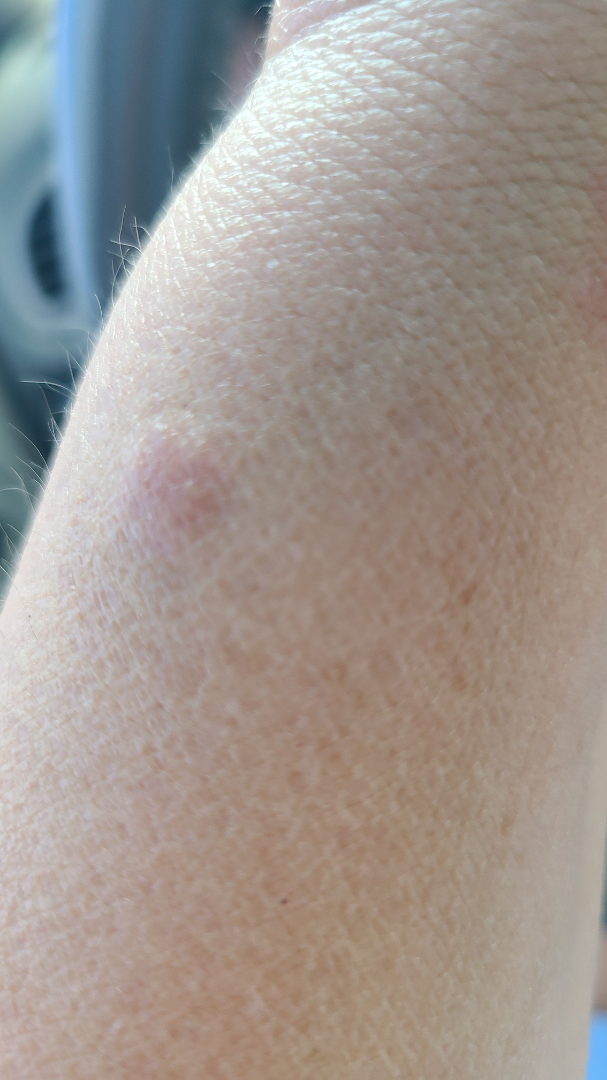The reviewer was unable to grade this case for skin condition. The leg, head or neck, top or side of the foot and arm are involved. Reported duration is three to twelve months. The patient indicates bothersome appearance. The lesion is described as raised or bumpy. An image taken at an angle. Self-categorized by the patient as a rash.